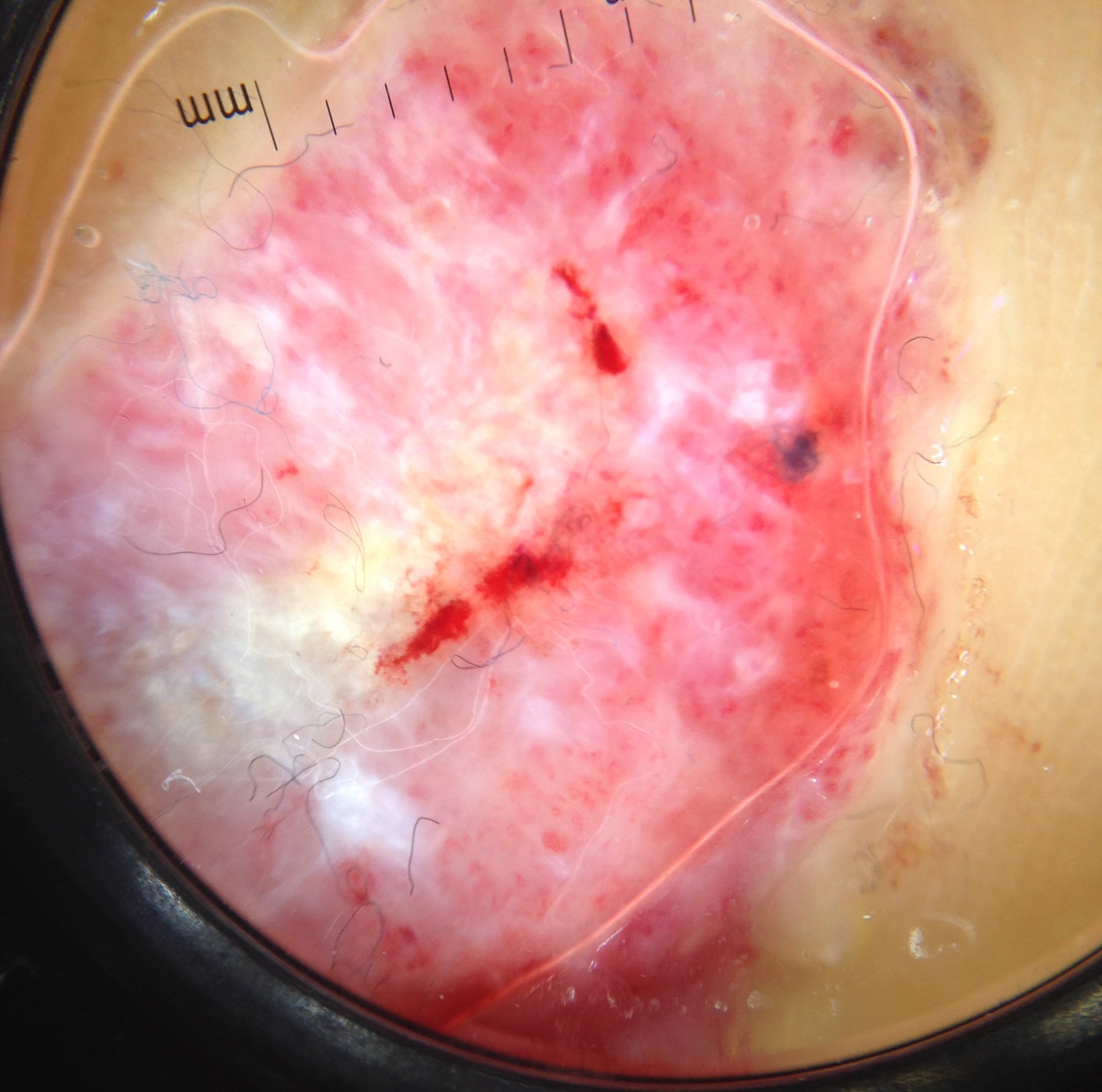A dermoscopic close-up of a skin lesion. Histopathology confirmed an acral nodular melanoma.